The affected area is the top or side of the foot and back of the hand · close-up view · reported lesion symptoms include itching · Fitzpatrick IV; non-clinician graders estimated Monk skin tone scale 5 (US pool) or 4 (India pool) · the patient described the issue as a rash · female contributor, age 18–29 · texture is reported as raised or bumpy · reported duration is more than one year: 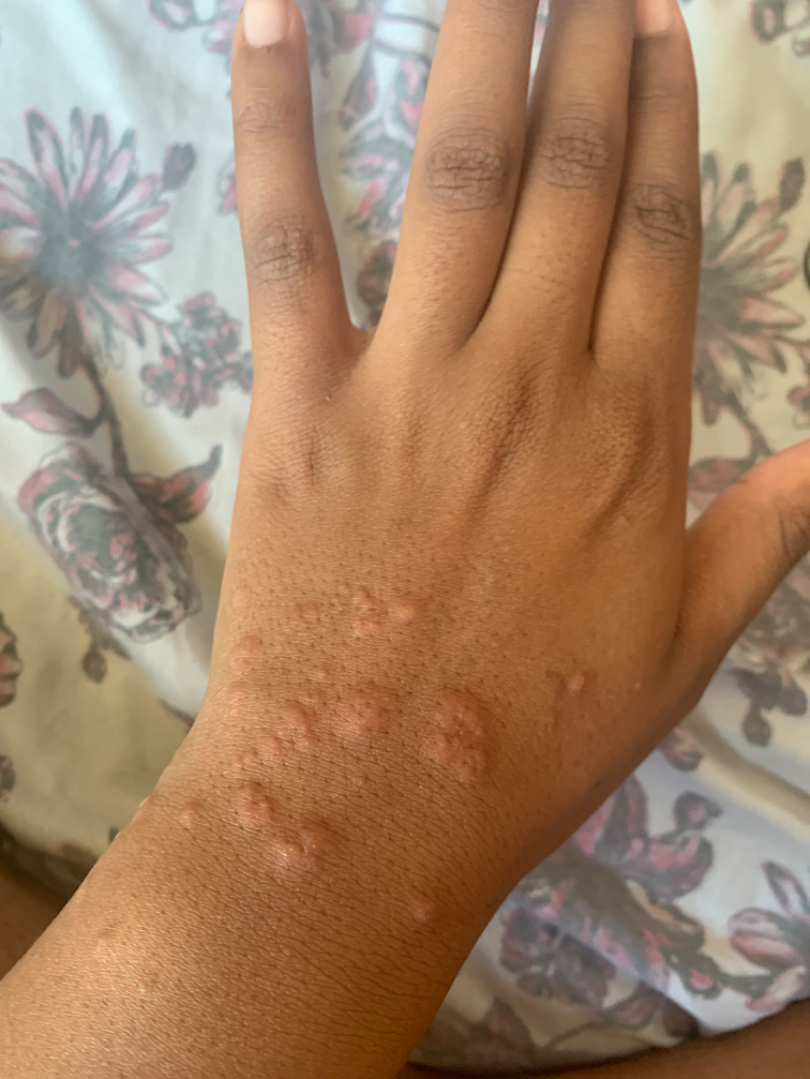Assessment: On teledermatology review: Diffuse xanthoma (possible); Benign tumor of dermis (possible); Insect Bite (possible); Acute dermatitis, NOS (possible); Collagenoma (possible); Verruca vulgaris (possible); Granulomatous disorder of the skin and subcutaneous tissue (possible).